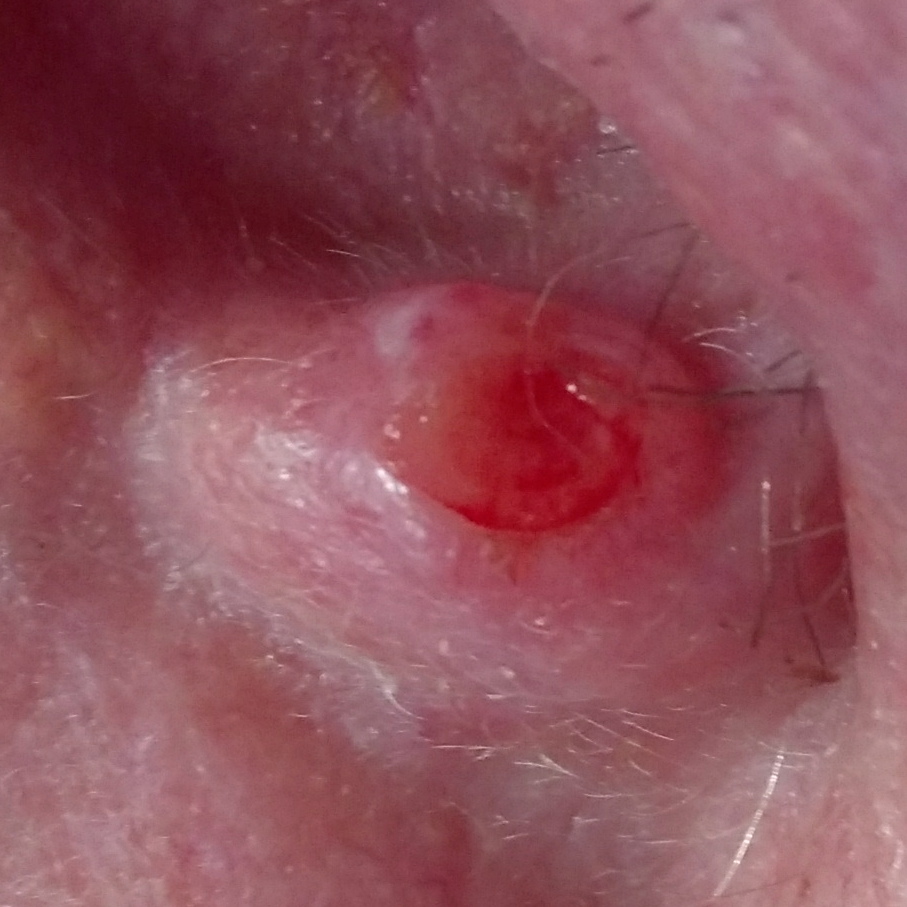Case:
– exposures · prior skin cancer (patient or family), prior malignancy (patient or family), no pesticide exposure
– patient · male, 84 years of age
– image · smartphone clinical photo
– anatomic site · an ear
– patient-reported symptoms · elevation, pain, itching, bleeding, growth / no change in appearance
– diagnostic label · basal cell carcinoma (biopsy-proven)